The patient was assessed as Fitzpatrick IV; a dermoscopic image of a skin lesion — 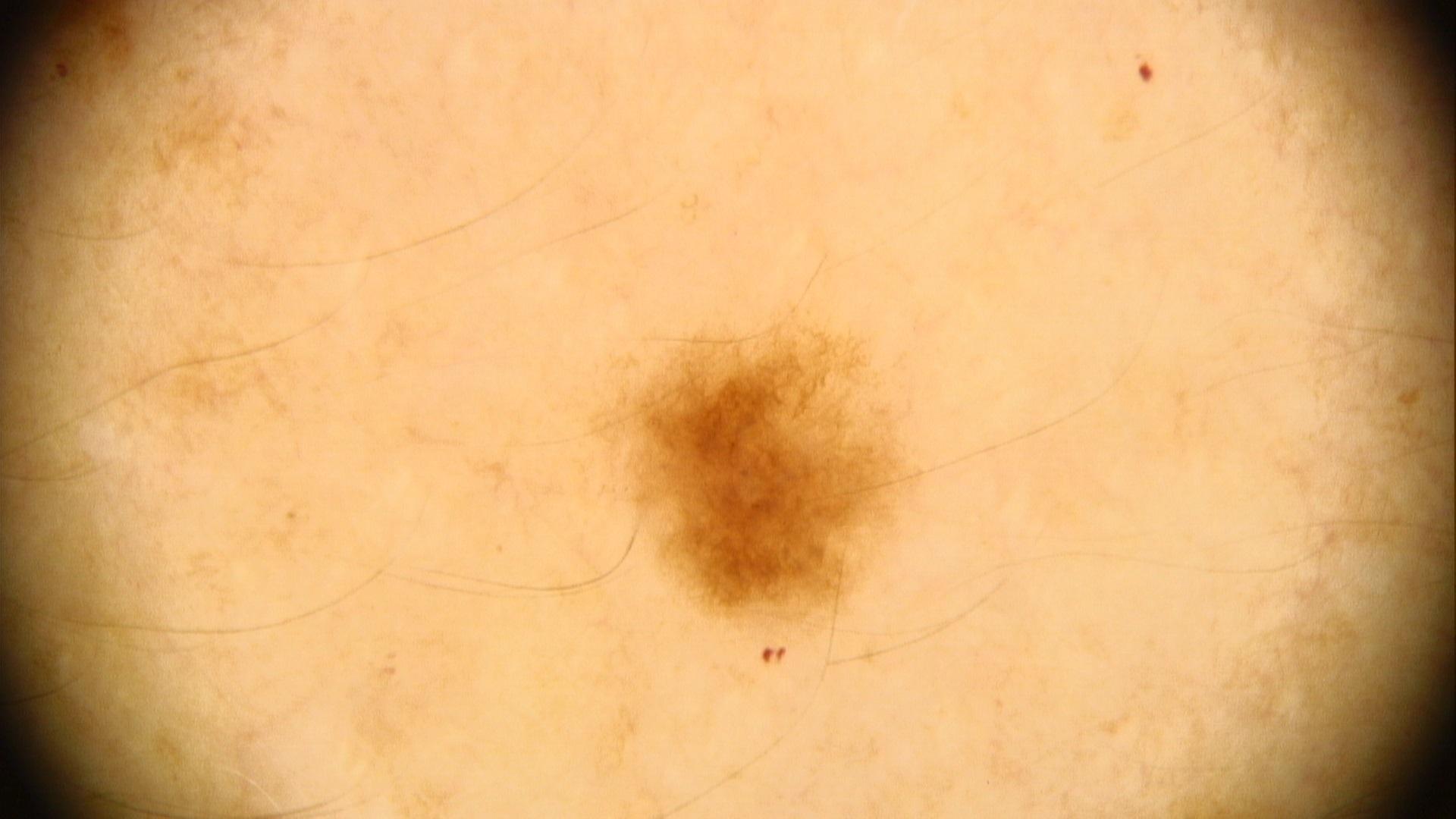assessment = Nevus.